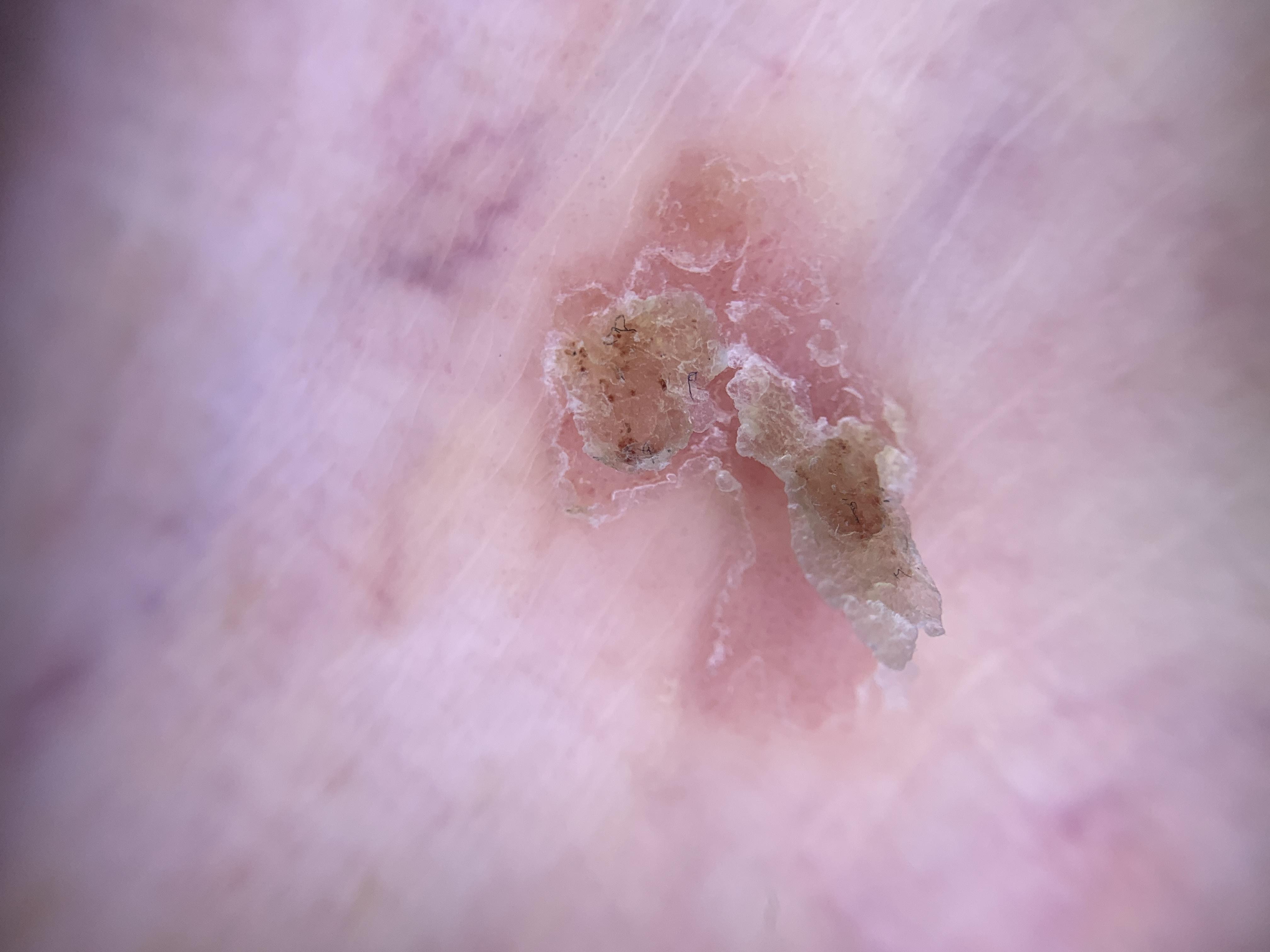Case:
• subject: female, aged 73 to 77
• modality: contact-polarized dermoscopy
• body site: a lower extremity
• diagnostic label: Squamous cell carcinoma (biopsy-proven)